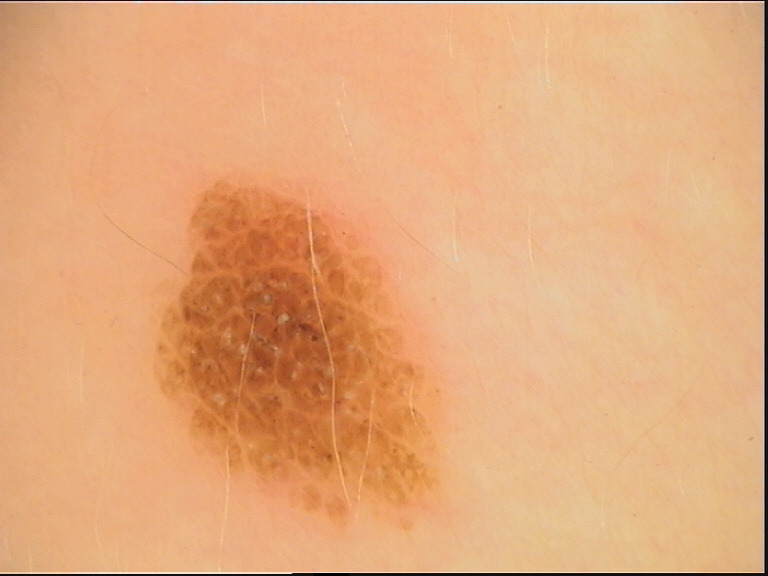Case:
A skin lesion imaged with a dermatoscope.
Impression:
Classified as a benign lesion — a dysplastic compound nevus.